This is a dermoscopic photograph of a skin lesion. The patient is a female about 15 years old — 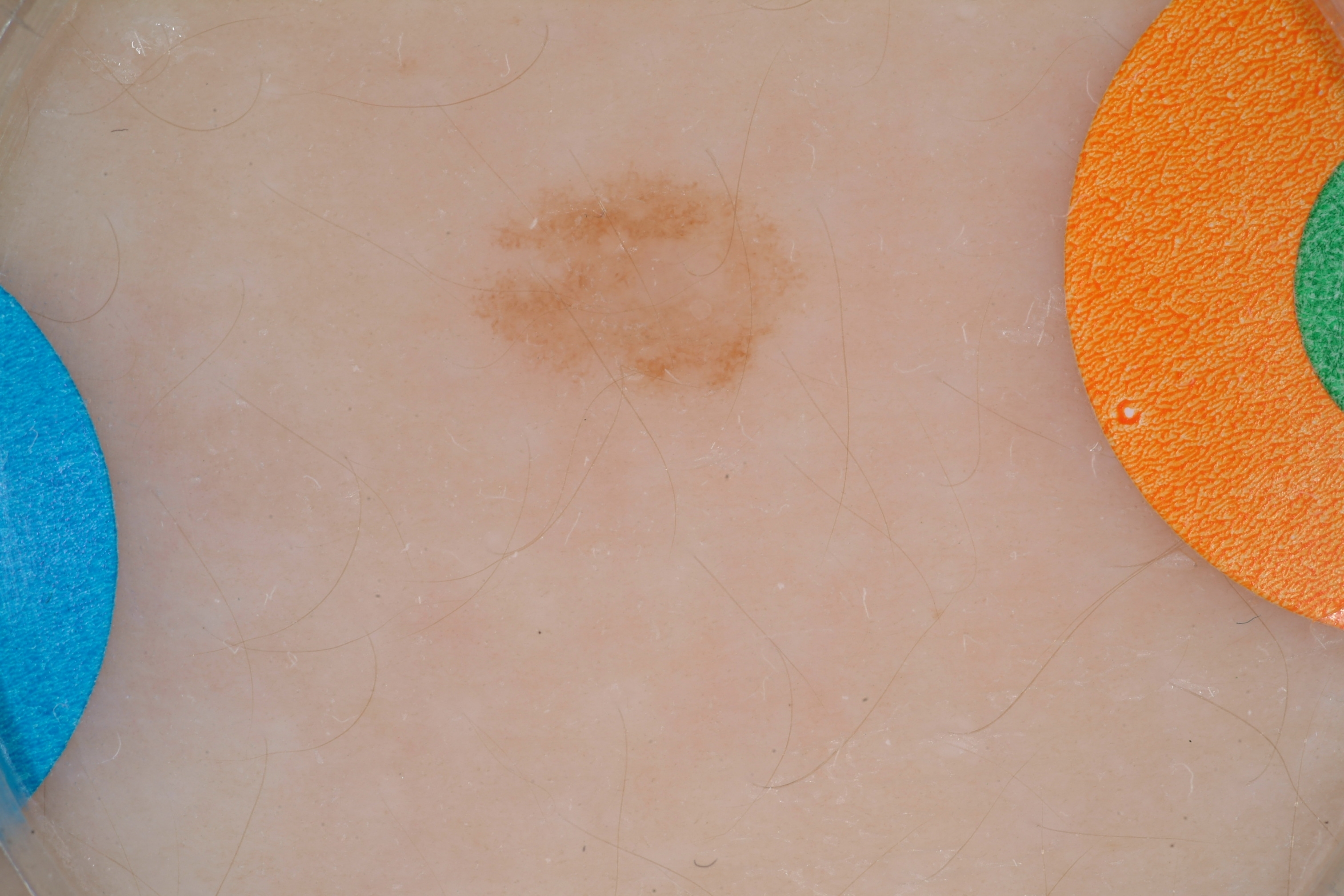Dermoscopically, the lesion shows no globules, pigment network, streaks, milia-like cysts, or negative network. The visible lesion spans <box>432, 143, 826, 418</box>. The diagnostic assessment was a melanocytic nevus, a benign lesion.